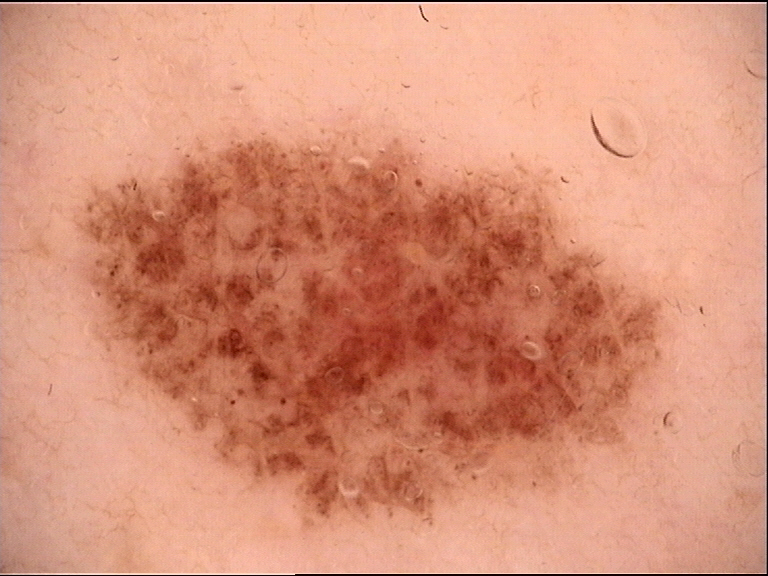Impression:
The diagnostic label was a benign lesion — a dysplastic junctional nevus.